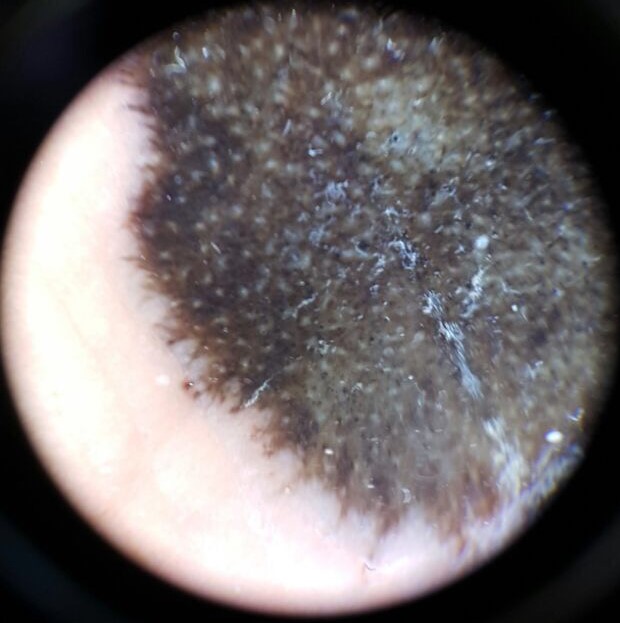* image type — dermatoscopy
* classification — banal
* diagnosis — congenital compound nevus (expert consensus)